FST III. A clinical close-up photograph of a skin lesion. By history, prior malignancy (patient or family), no pesticide exposure, and no prior skin cancer (patient or family). A female subject 73 years of age — 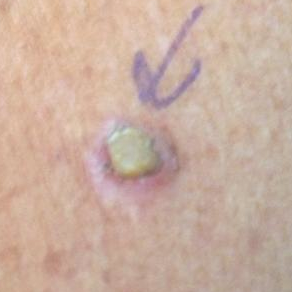Q: Where on the body is the lesion?
A: an arm
Q: Lesion size?
A: 10 × 7 mm
Q: What symptoms does the patient report?
A: elevation, growth
Q: What is the diagnosis?
A: squamous cell carcinoma (biopsy-proven)